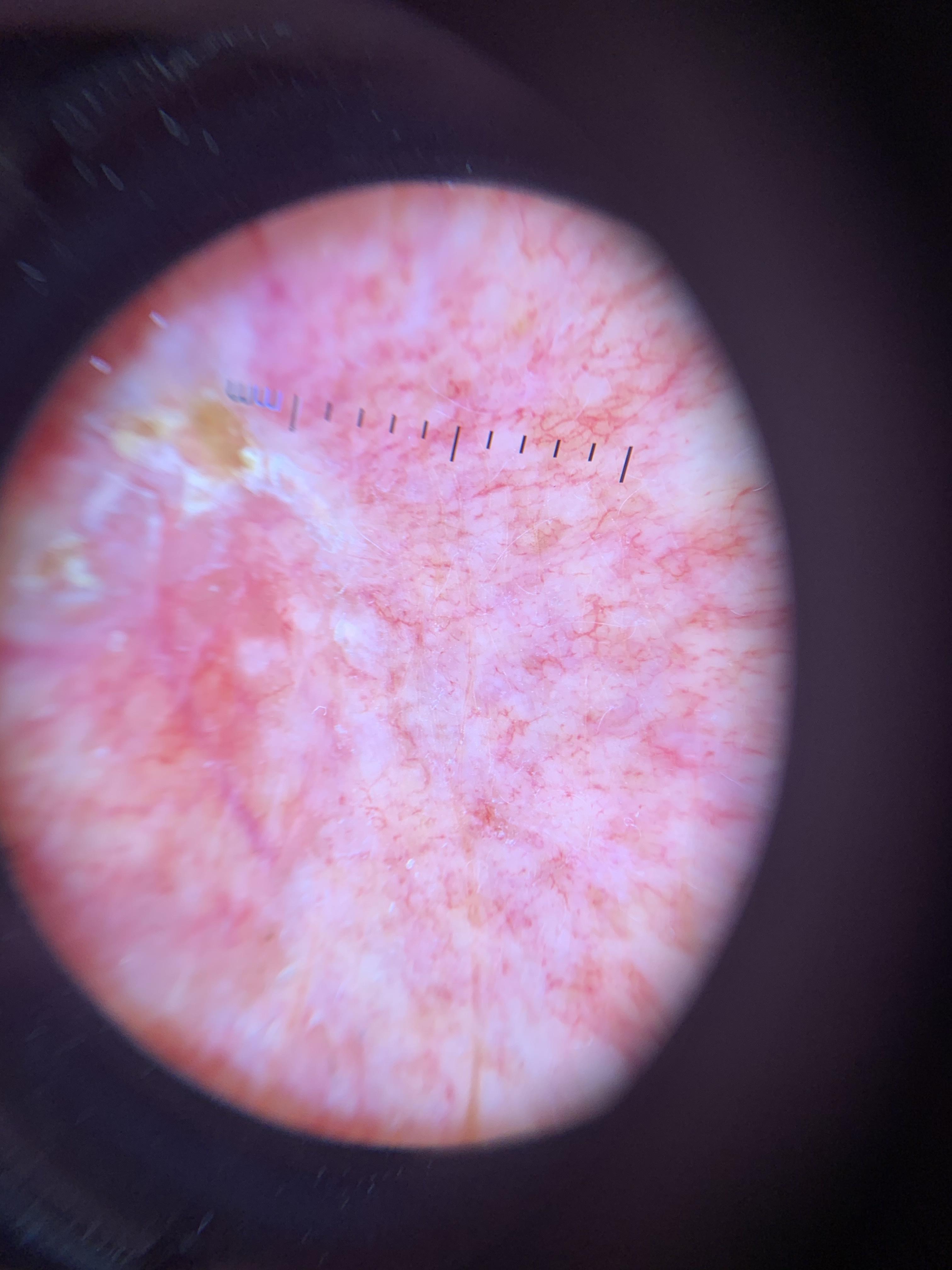A contact-polarized dermoscopy image of a skin lesion.
A male subject in their 70s.
FST II.
The lesion was found on the head or neck.
The biopsy diagnosis was a squamous cell carcinoma.